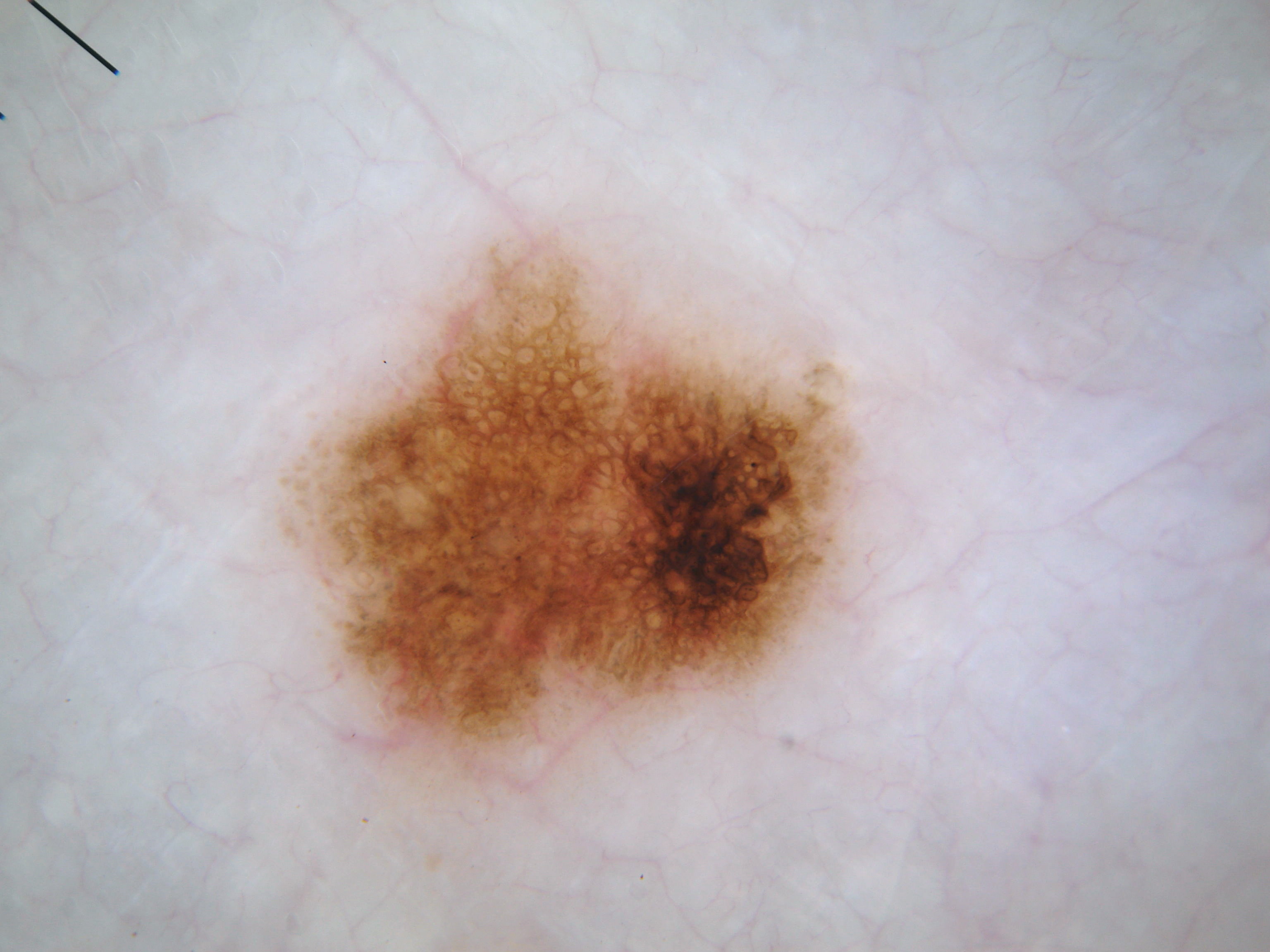{"image": {"modality": "dermoscopy"}, "lesion_location": {"bbox_xyxy": [279, 235, 859, 809]}, "diagnosis": {"name": "melanocytic nevus", "malignancy": "benign", "lineage": "melanocytic", "provenance": "clinical"}}